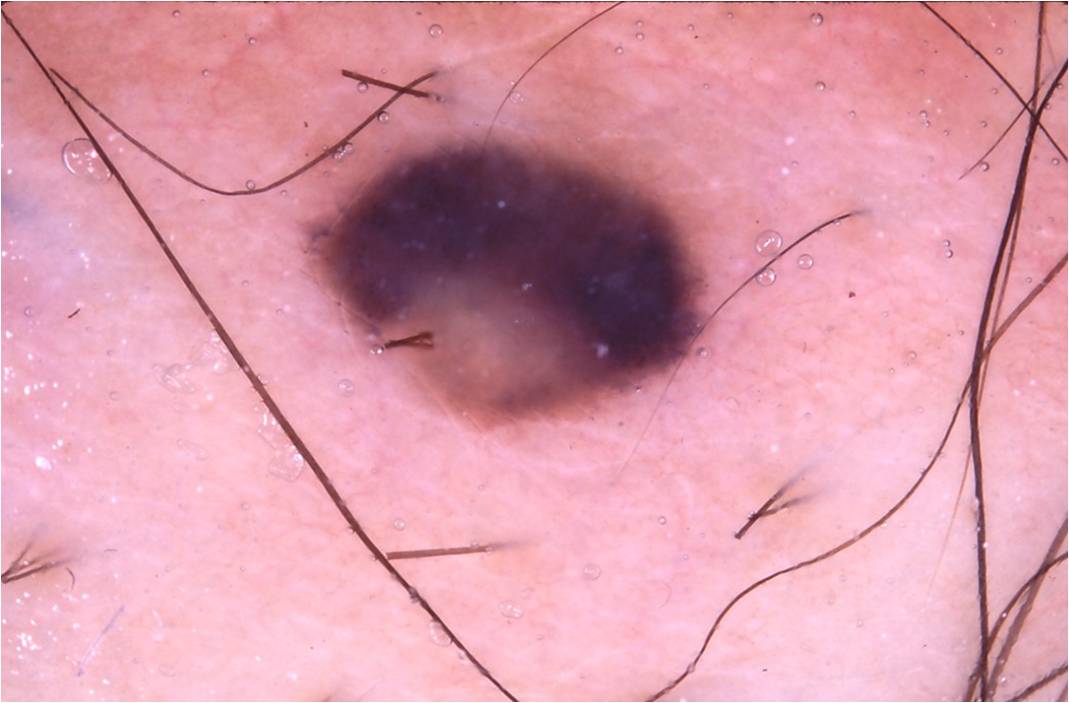A skin lesion imaged with a dermatoscope.
A male subject approximately 25 years of age.
In (x1, y1, x2, y2) order, the visible lesion spans 296 126 711 433.
Dermoscopic examination shows no milia-like cysts, pigment network, negative network, globules, or streaks.
Clinically diagnosed as a melanocytic nevus.